A male patient in their 60s · contact-polarized dermoscopy of a skin lesion: 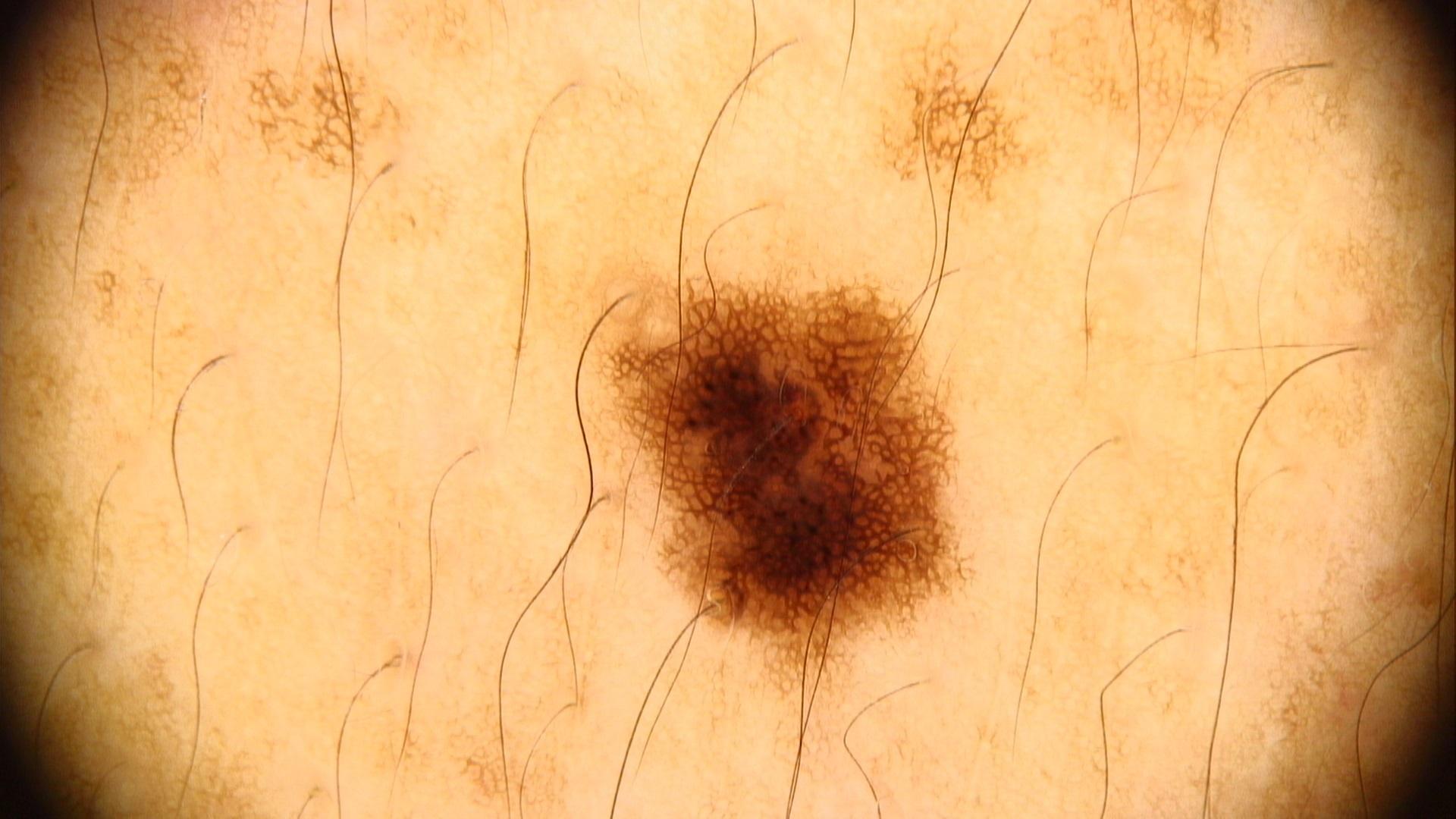The lesion is on the trunk (the posterior trunk).
Clinically diagnosed as a nevus.